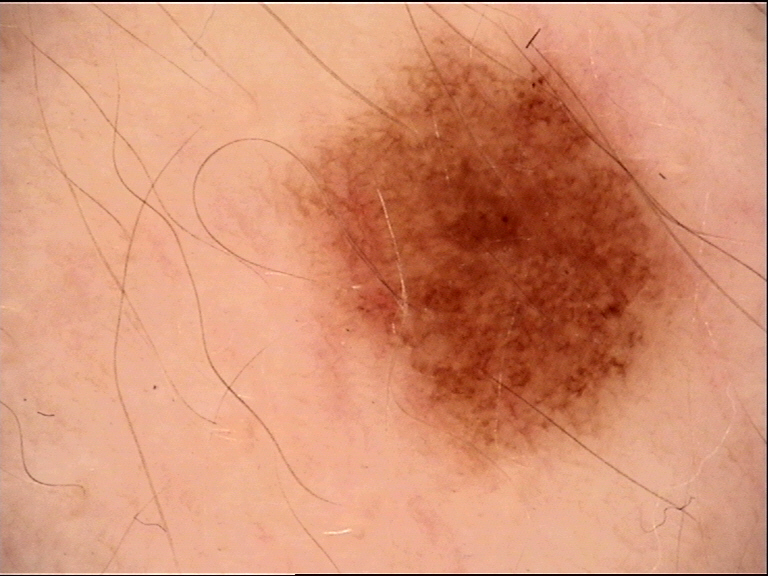image type=dermatoscopy
class=junctional nevus (expert consensus)